A female subject 26 years of age; a dermoscopy image of a skin lesion; acquired for a research image collection, with no referral diagnosis.
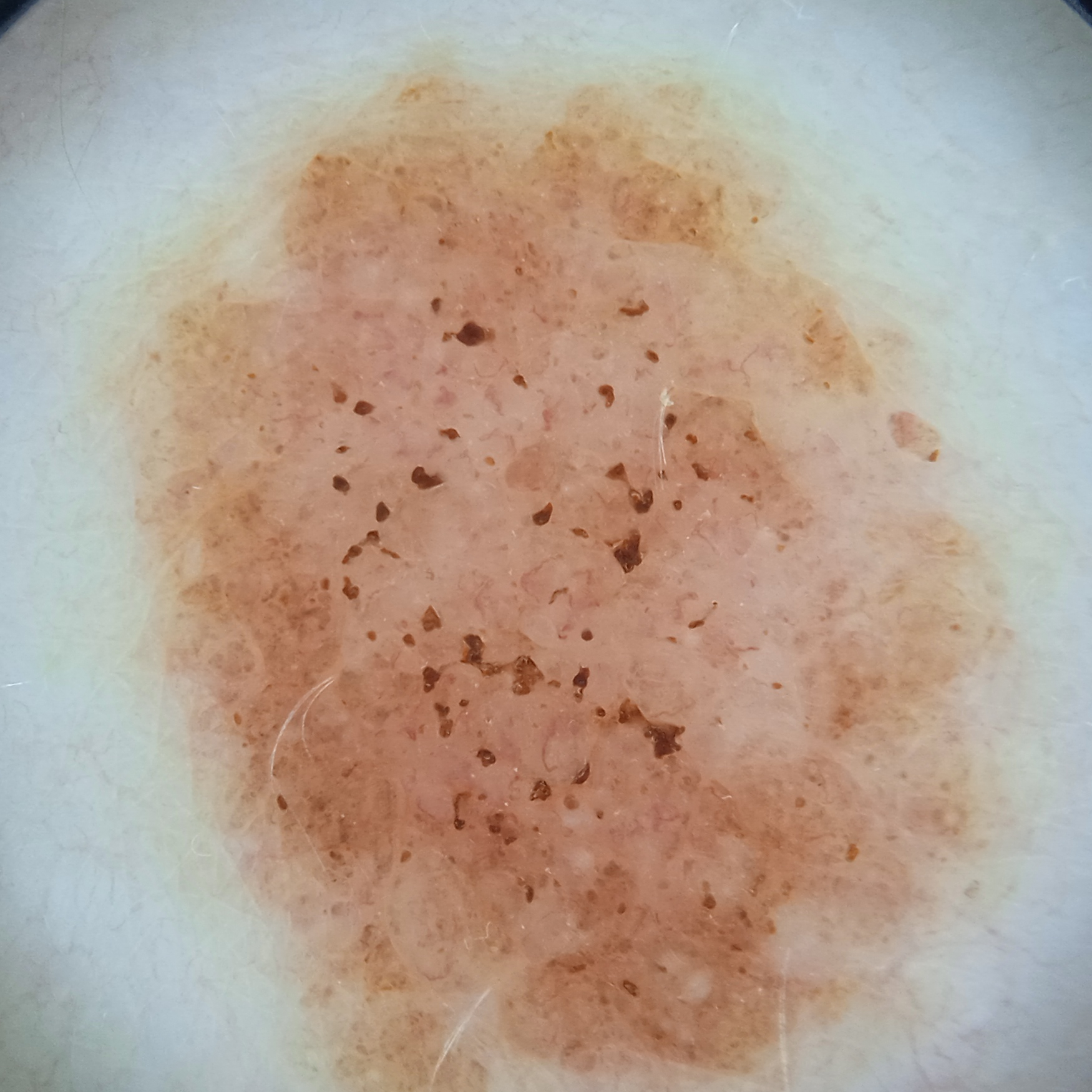site — the torso | size — 13 mm | assessment — melanocytic nevus (dermatologist consensus).